Dermoscopy of a skin lesion.
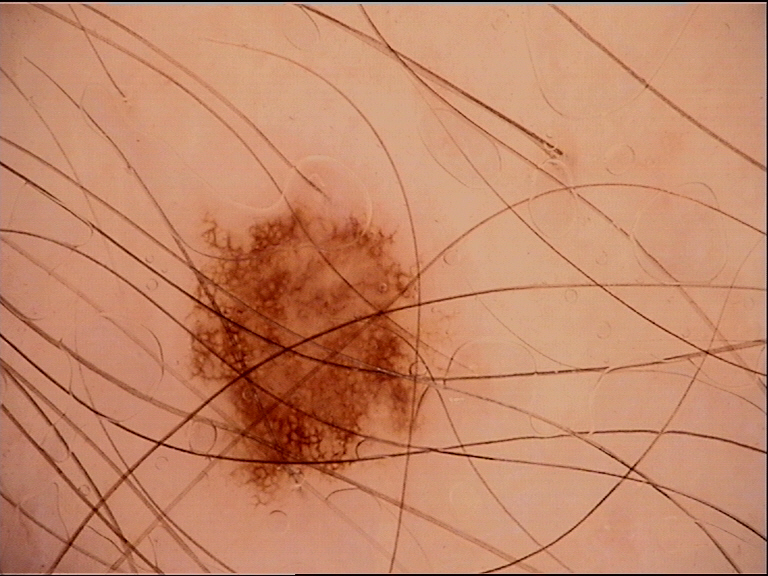Impression: The diagnosis was a dysplastic junctional nevus.